A dermatoscopic image of a skin lesion.
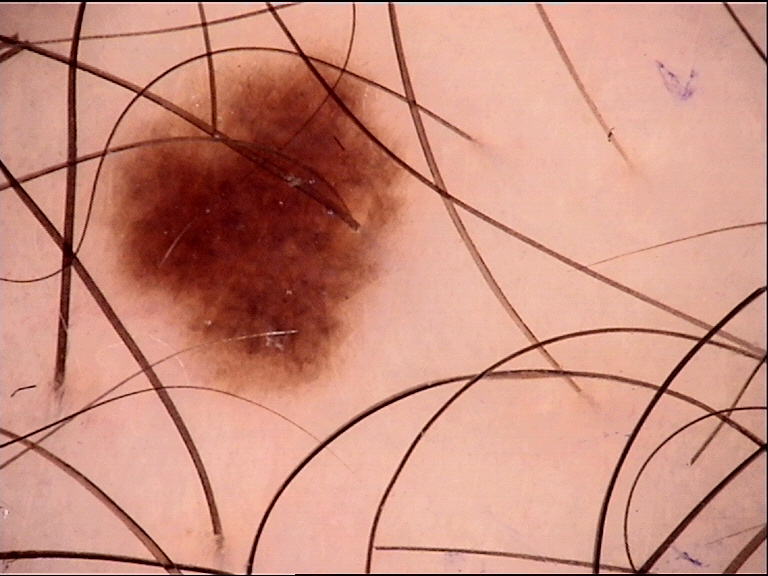| key | value |
|---|---|
| diagnosis | dysplastic junctional nevus (expert consensus) |